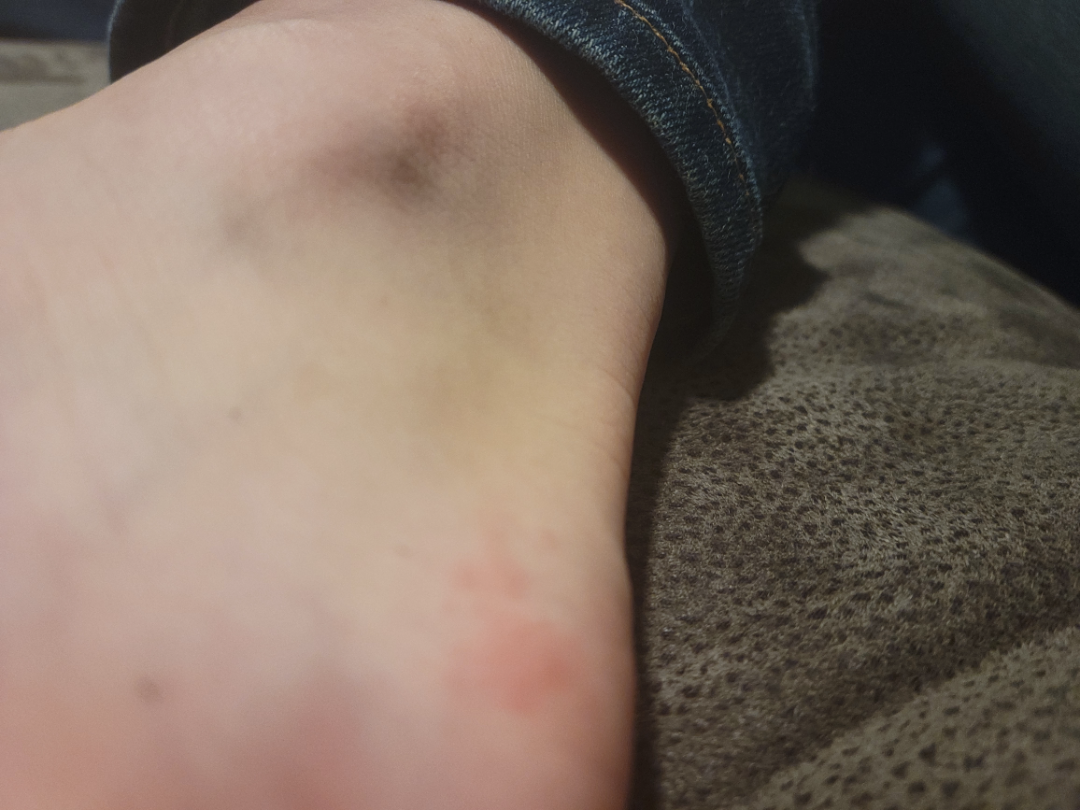Assessment:
Diagnostic features were not clearly distinguishable in this photograph.
Clinical context:
The lesion is associated with itching. Present for less than one week. The patient is a male aged 18–29. This image was taken at an angle. The patient described the issue as a rash. The affected area is the top or side of the foot. The lesion is described as raised or bumpy.